The patient notes the lesion is raised or bumpy and rough or flaky · a close-up photograph · the patient is a female aged 30–39 · the patient also reports joint pain · located on the head or neck and back of the hand · the lesion is associated with burning and pain · self-categorized by the patient as a rash.
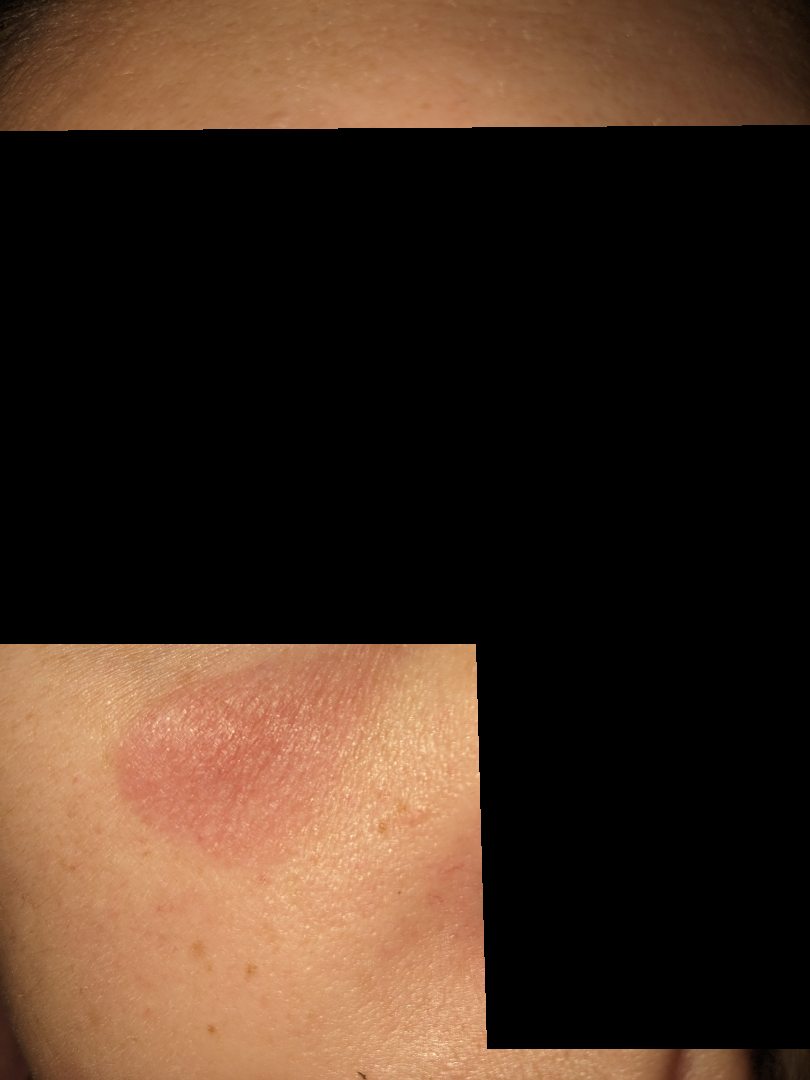The case was difficult to assess from the available photograph.